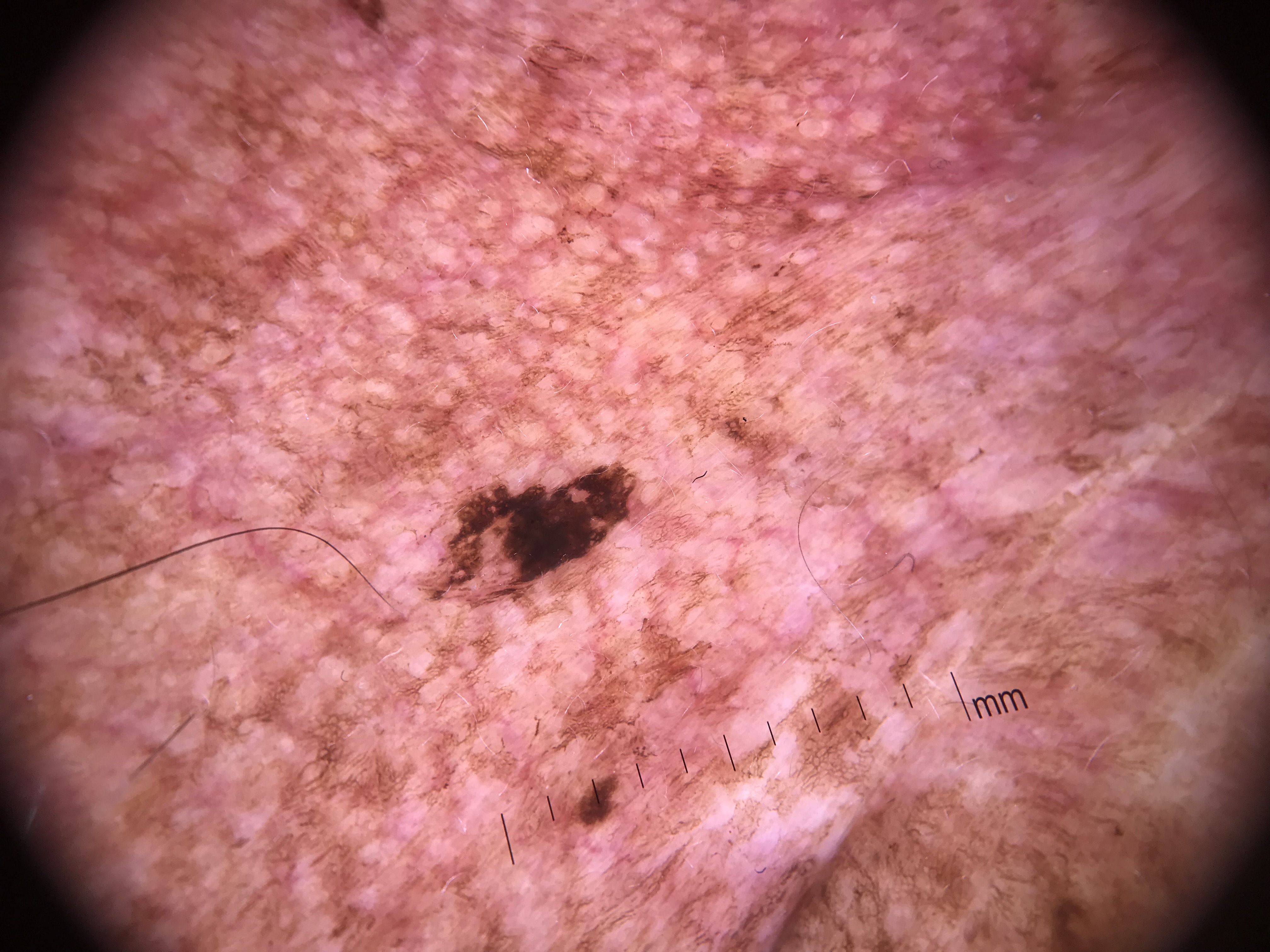{"diagnosis": {"name": "lentigo maligna", "code": "lm", "malignancy": "malignant", "super_class": "melanocytic", "confirmation": "histopathology"}}